The photograph was taken at an angle; the lesion involves the arm: 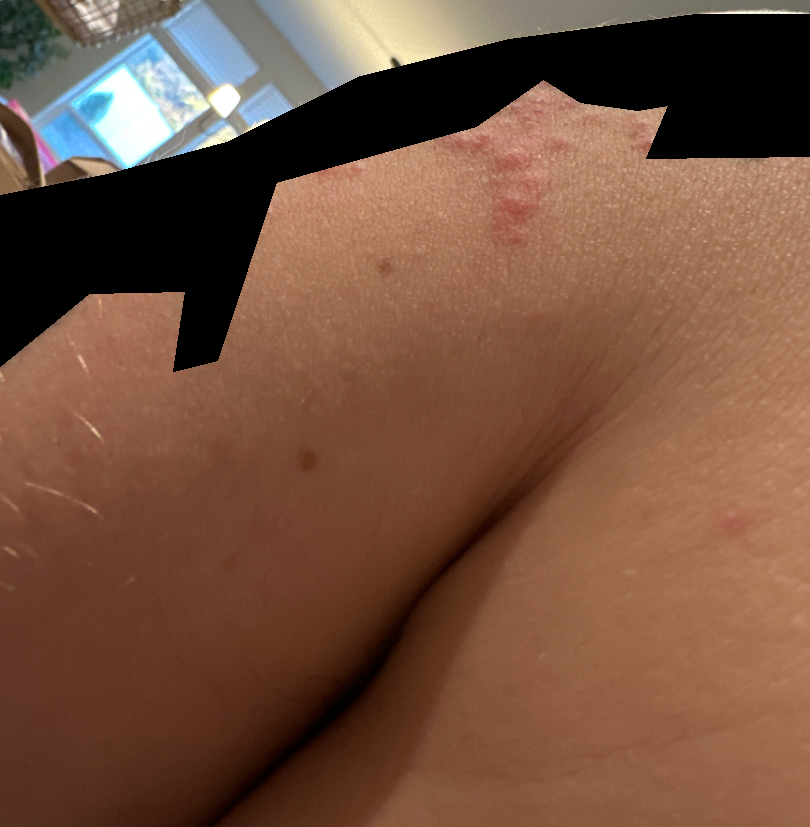assessment — not assessable
symptoms — bothersome appearance
constitutional symptoms — none reported
history — less than one week
patient describes the issue as — a rash